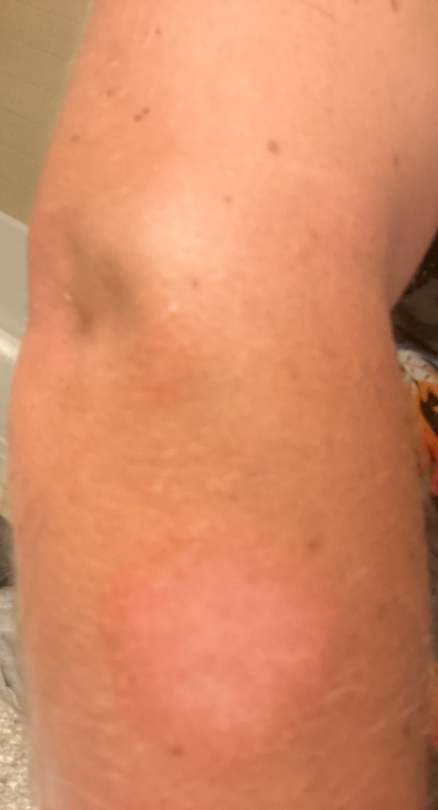Patient information: Reported duration is one to four weeks. The patient considered this a rash. The lesion is described as raised or bumpy. A close-up photograph. Reported lesion symptoms include itching, bothersome appearance and enlargement. Male contributor, age 30–39. The affected area is the arm. The patient indicates associated joint pain, mouth sores, fatigue and chills. Review: The reviewing dermatologist's impression was: favoring Tinea; also on the differential is Eczema; less likely is Erythema annulare centrifugum.